A dermatoscopic image of a skin lesion.
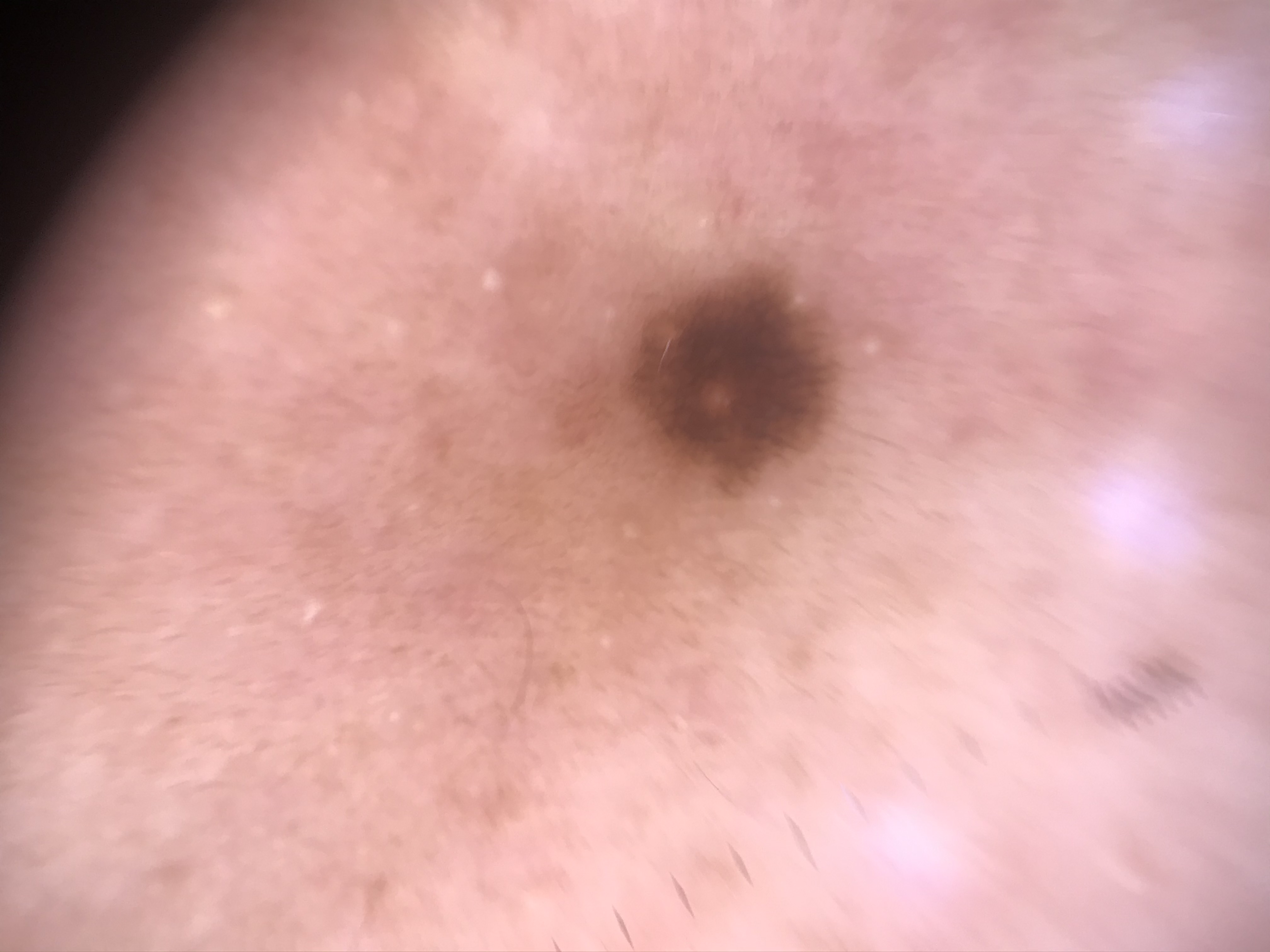This is a banal lesion. The diagnosis was a junctional nevus.